A dermatoscopic image of a skin lesion: 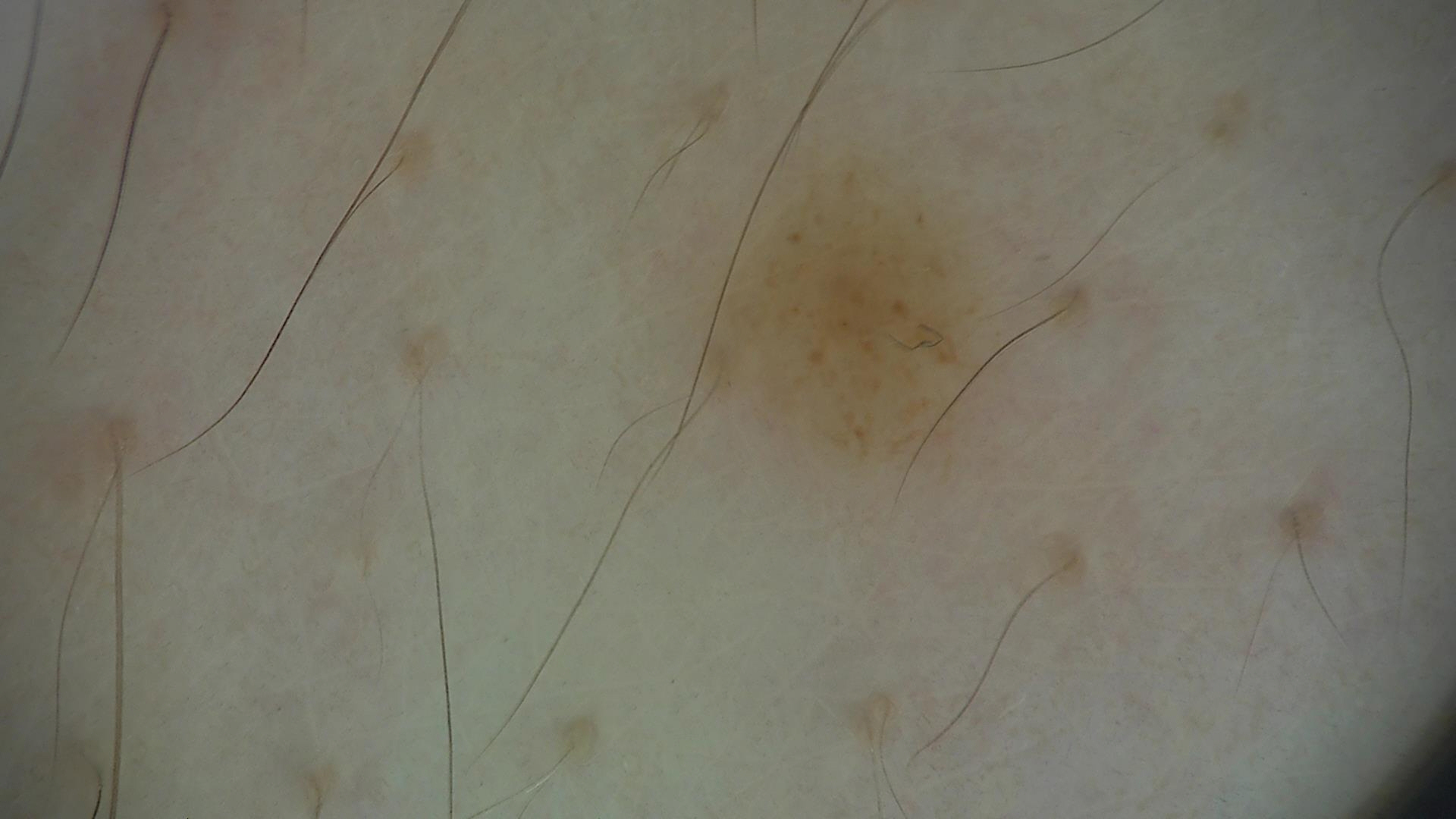– diagnosis: dysplastic junctional nevus (expert consensus)